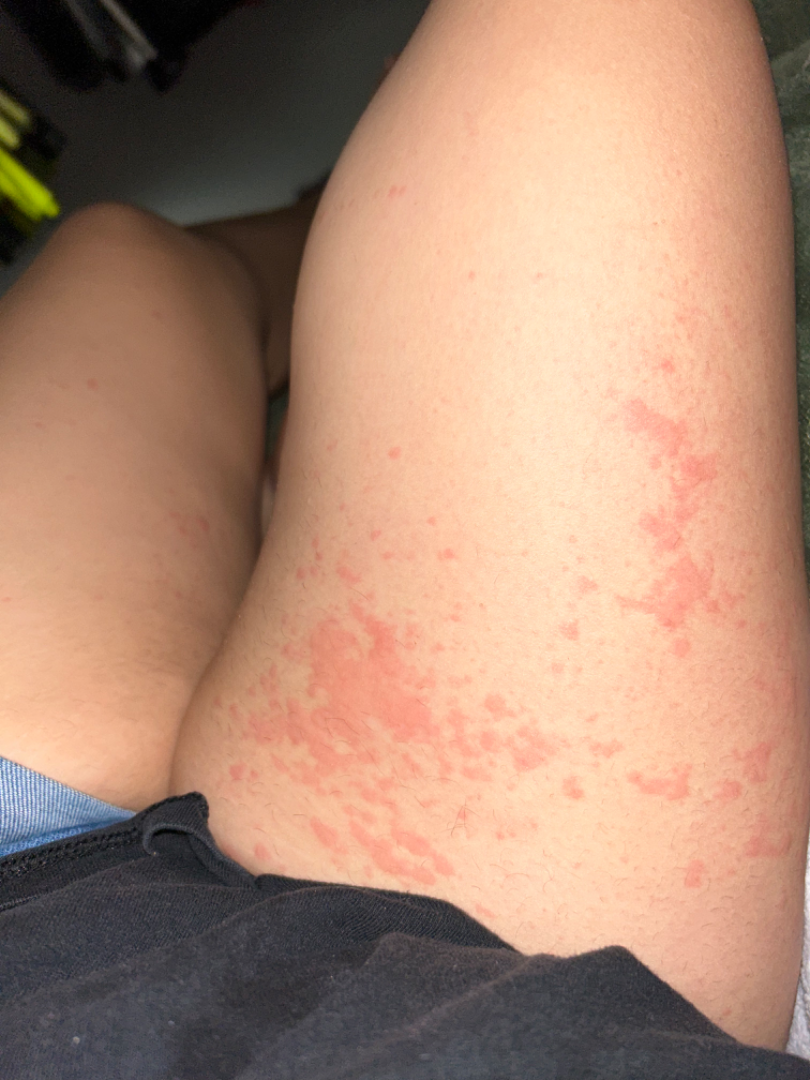Clinical context:
The arm, leg, palm, front of the torso and top or side of the foot are involved. The photo was captured at a distance. The patient is a female aged 18–29. Reported duration is less than one week.
Assessment:
The reviewing dermatologists' impression was: Urticaria (primary); Allergic Contact Dermatitis (considered); Hypersensitivity (unlikely).